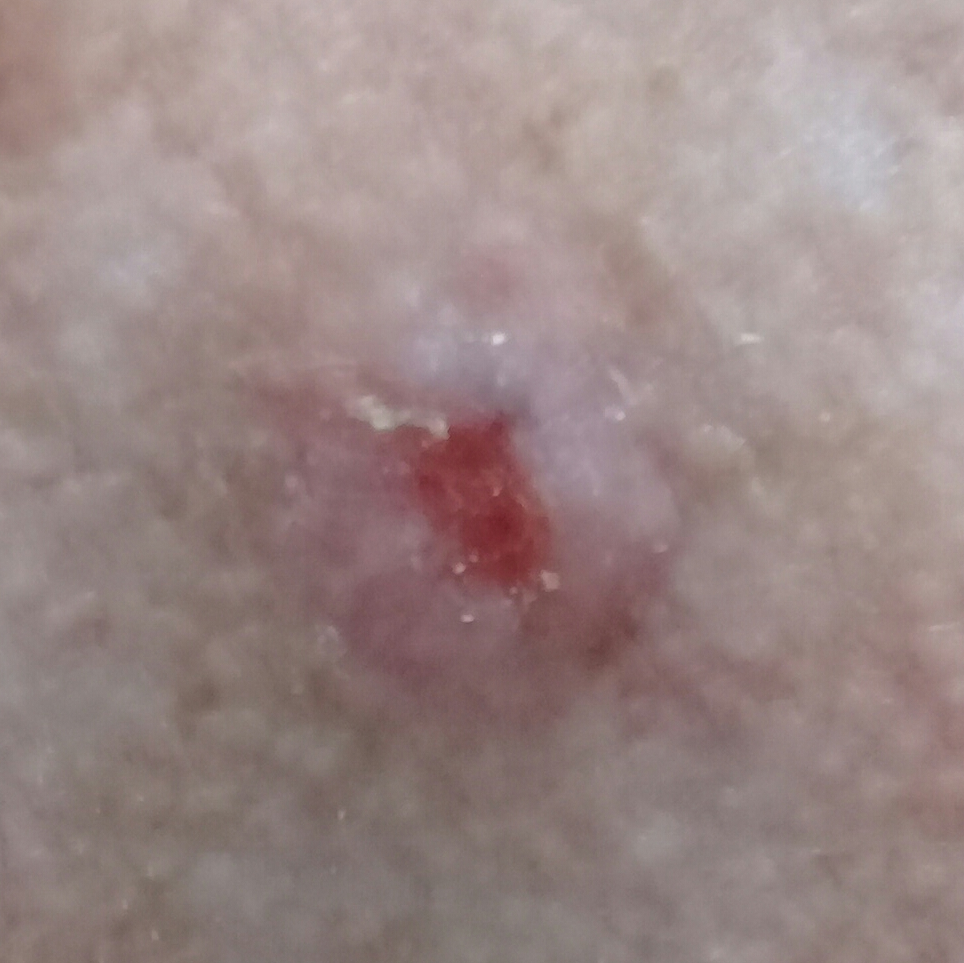By history, alcohol use, prior skin cancer (patient or family), prior malignancy (patient or family), and no tobacco use. FST III. A clinical photograph showing a skin lesion. A male patient 63 years of age. The lesion is on the chest. The lesion measures 8 × 8 mm. The patient reports that the lesion is elevated, has bled, hurts, and itches. Biopsy-confirmed as a basal cell carcinoma.